A dermoscopy image of a single skin lesion:
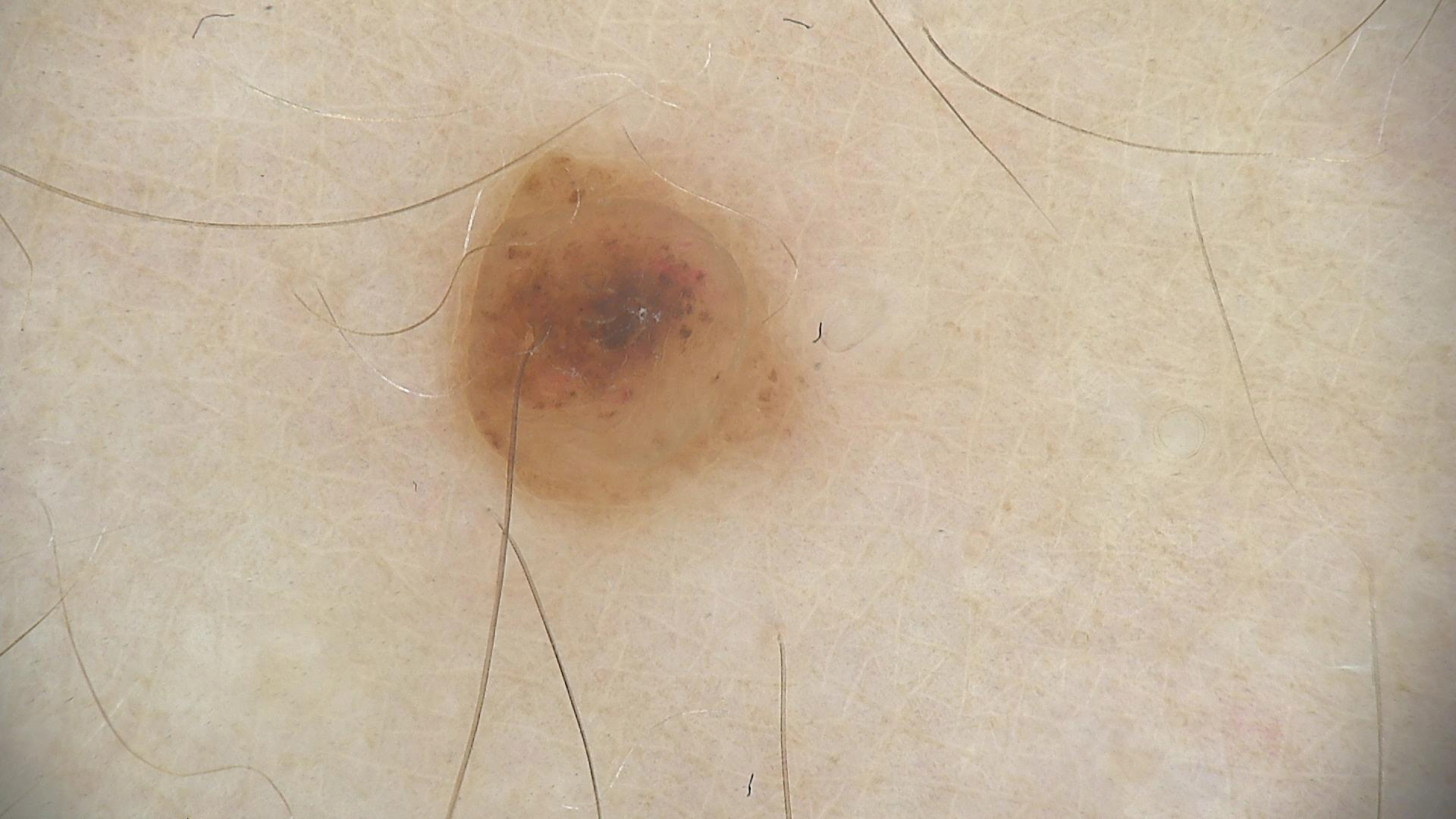Classified as a banal lesion — a dermal nevus.